Dermoscopy of a skin lesion:
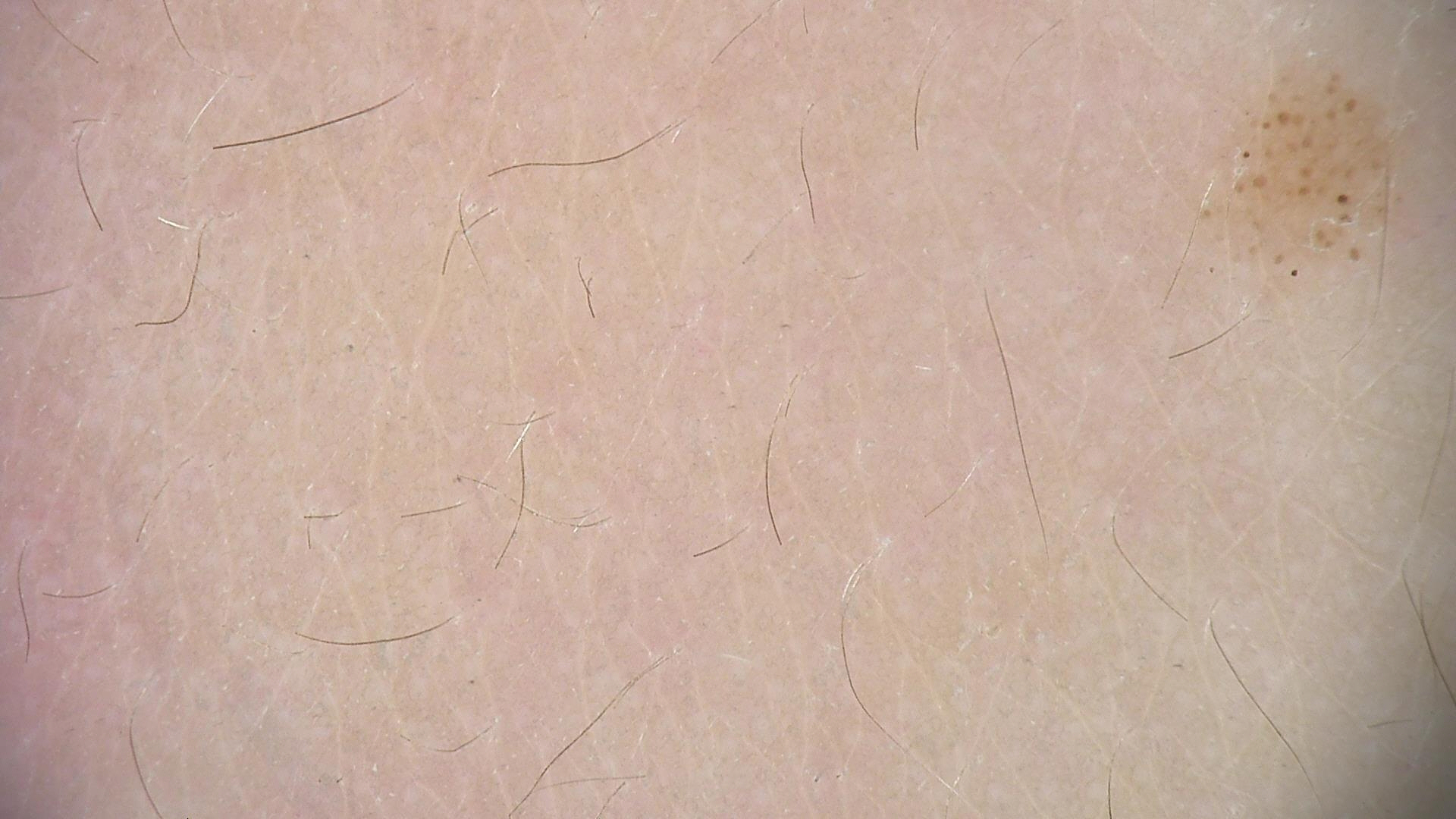diagnostic label: dysplastic junctional nevus (expert consensus).